A dermoscopic image of a skin lesion: 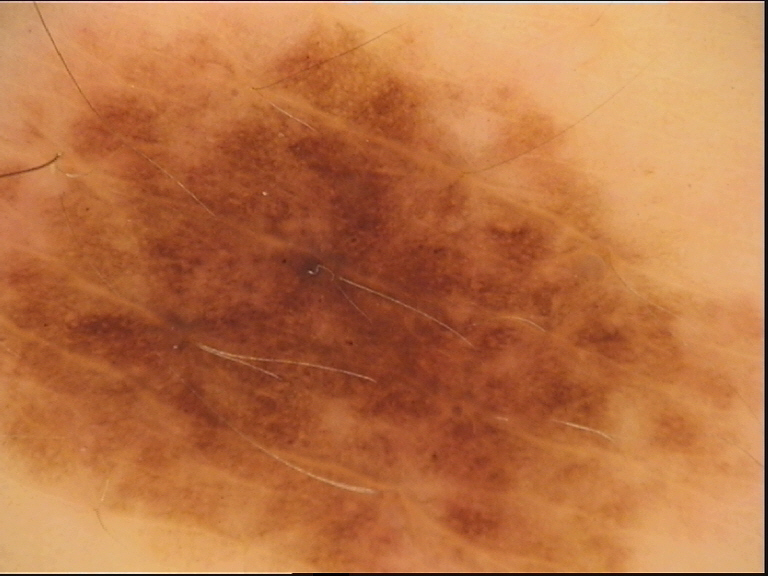The diagnostic label was a dysplastic compound nevus.